The subject is a male aged 43-47. A dermoscopic image of a skin lesion.
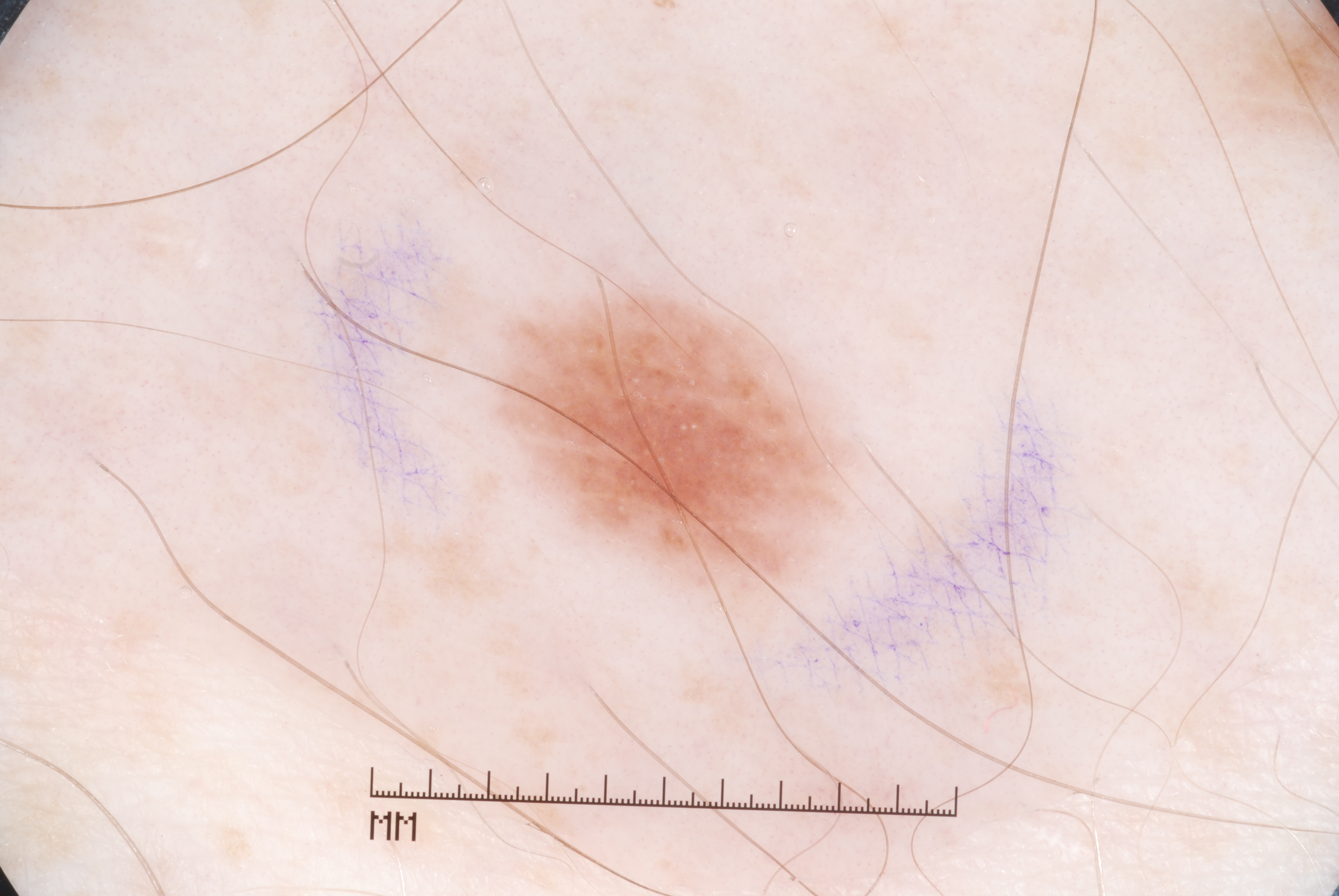Image and clinical context: In (x1, y1, x2, y2) order, the lesion is located at 502 287 848 595. A small lesion within a wider field of skin. The dermoscopic pattern shows milia-like cysts. Conclusion: Expert review diagnosed this as a melanocytic nevus.